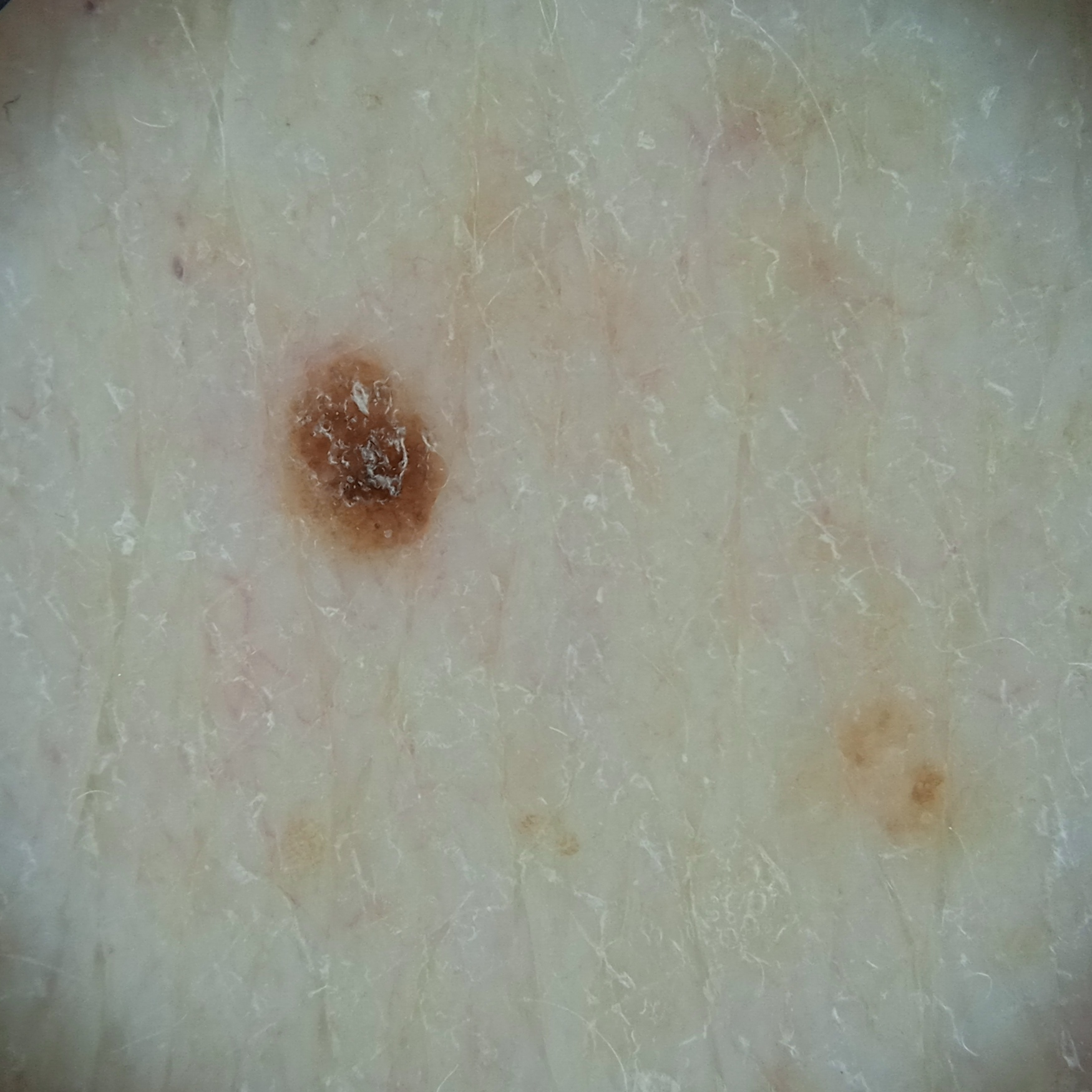Q: What is the imaging modality?
A: dermoscopic image
Q: Why was this imaged?
A: research study (no referral diagnosis)
Q: Patient demographics?
A: male, 83 years old
Q: Where is the lesion?
A: the back
Q: Lesion size?
A: 2.5 mm
Q: What was the diagnosis?
A: seborrheic keratosis (dermatologist consensus)